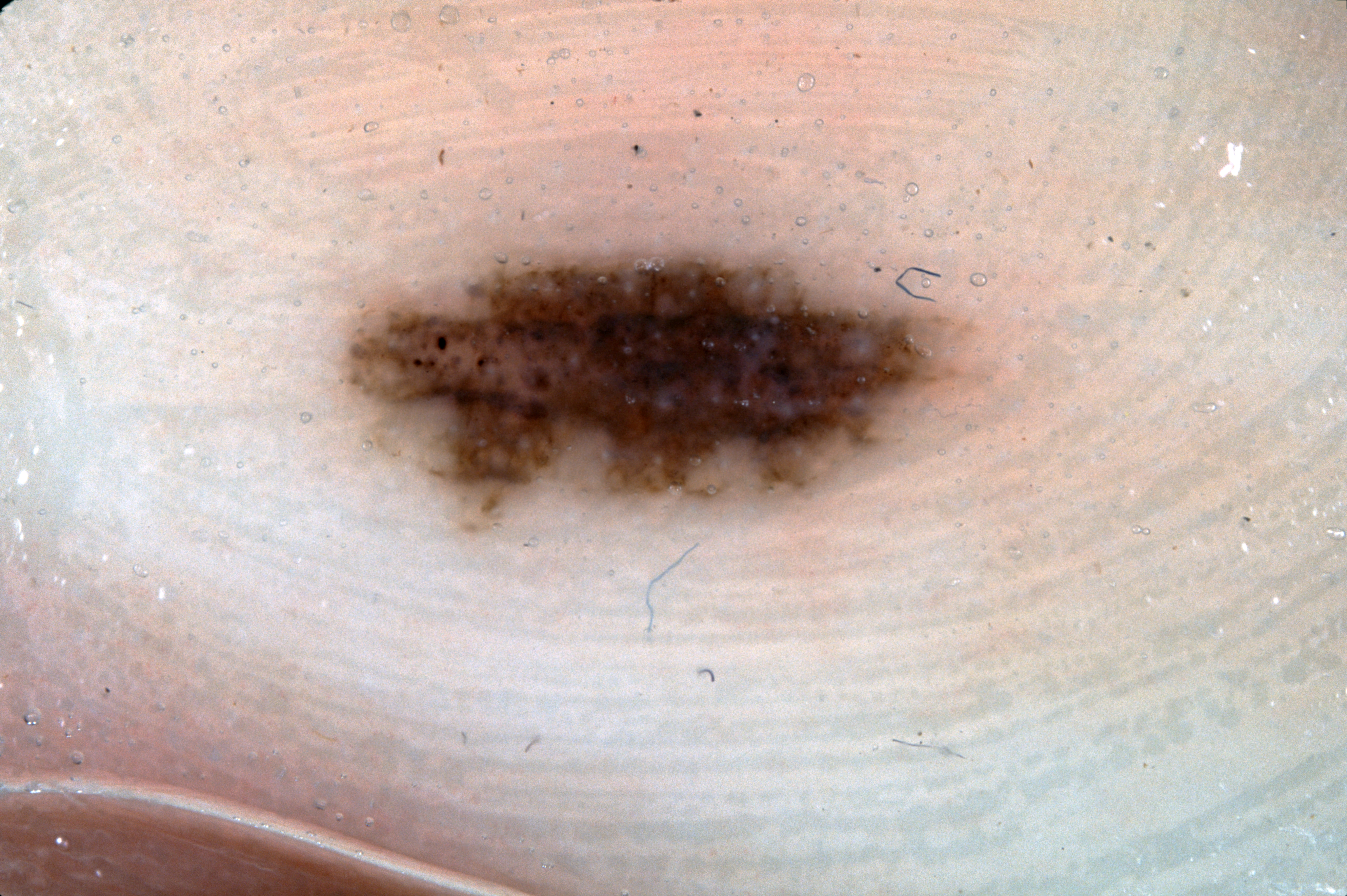image type = dermoscopy of a skin lesion; lesion size = moderate; absent dermoscopic findings = negative network, milia-like cysts, streaks, and pigment network; bounding box = (348, 250, 958, 518); impression = a melanocytic nevus.